Dermoscopy of a skin lesion:
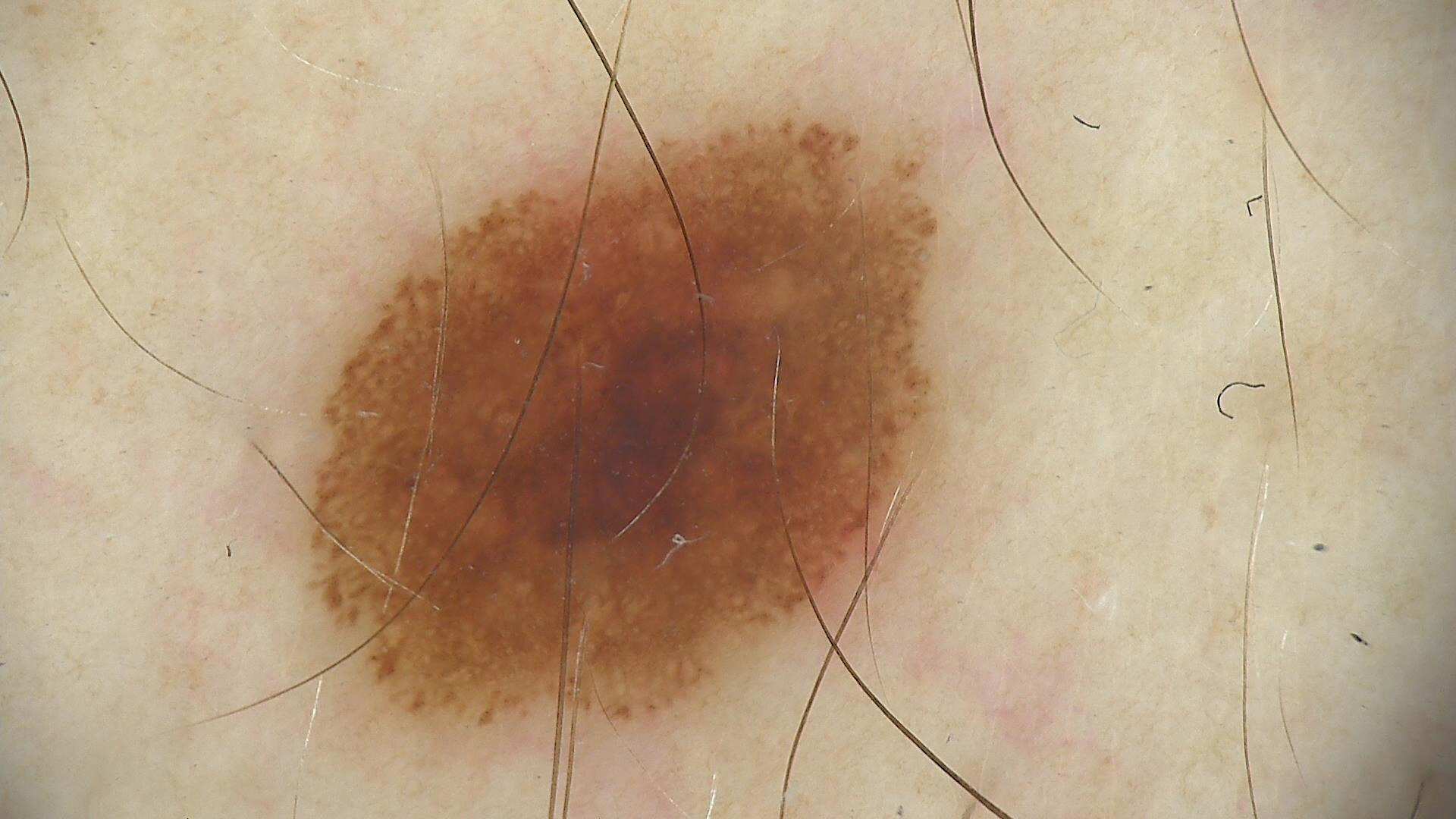Consistent with a banal lesion — a compound nevus.